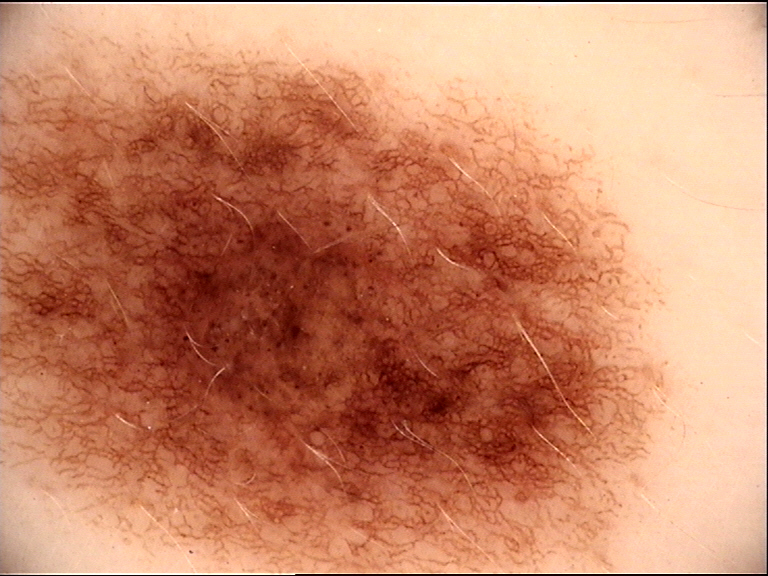Classified as a dysplastic junctional nevus.